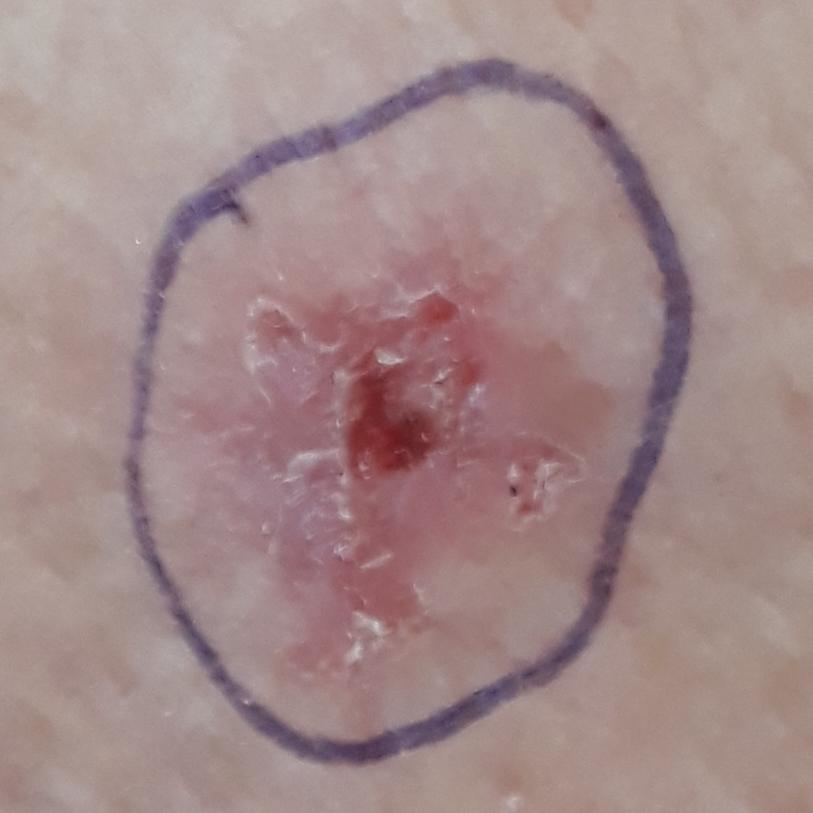A female subject aged 86.
Recorded as Fitzpatrick phototype II.
A clinical photo of a skin lesion taken with a smartphone.
History notes prior malignancy (patient or family).
The lesion involves an arm.
The lesion is roughly 14 by 12 mm.
The patient reports that the lesion itches, but has not changed and has not grown.
The biopsy diagnosis was a skin cancer — a basal cell carcinoma.